Male subject, age 18–29; the photograph is a close-up of the affected area; located on the arm: 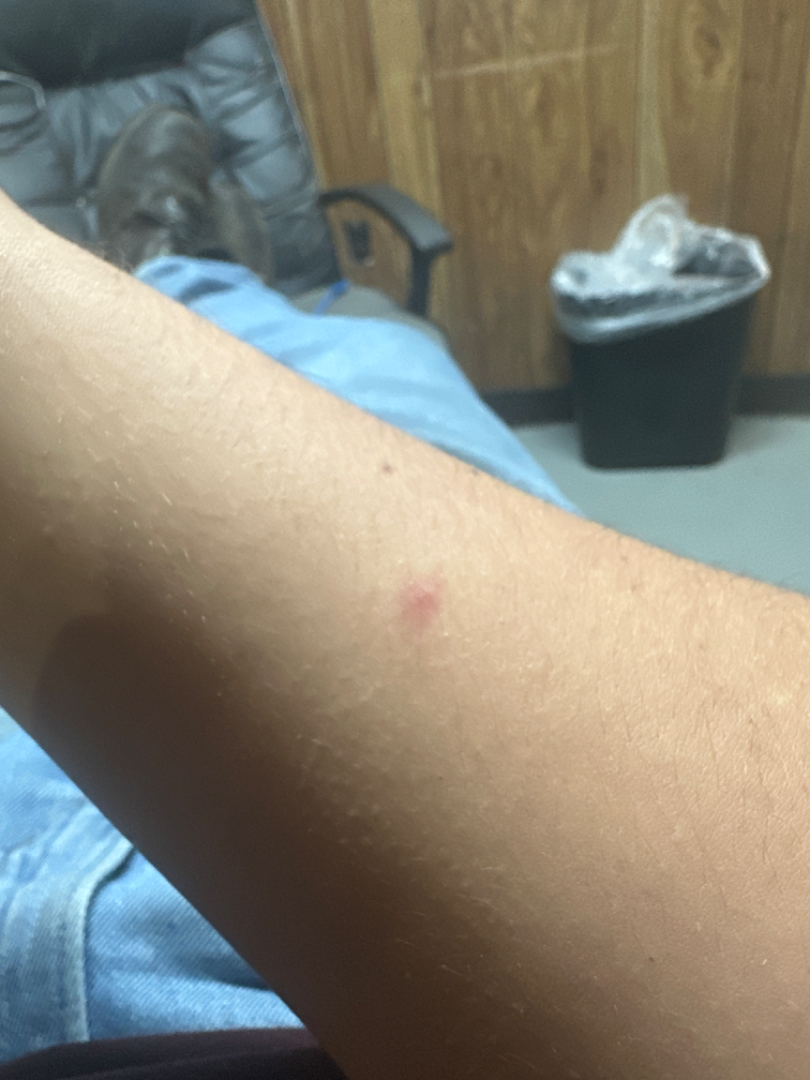  duration: about one day
  texture: flat
  systemic_symptoms: none reported
  differential:
    leading:
      - Insect Bite
    considered:
      - Abscess
      - Cyst